The photograph is a close-up of the affected area, the affected area is the head or neck, the contributor reports enlargement and itching, the patient described the issue as a rash.
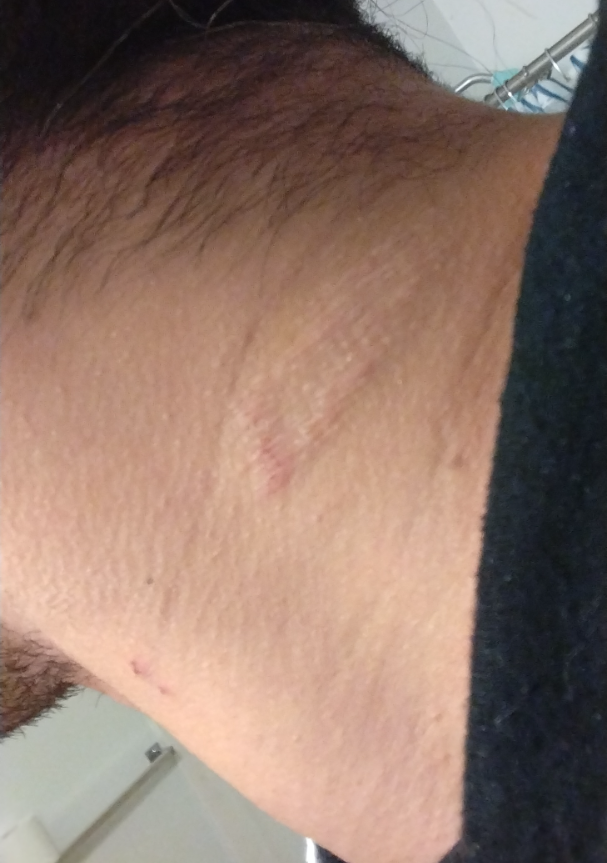Impression: The case was difficult to assess from the available photograph.